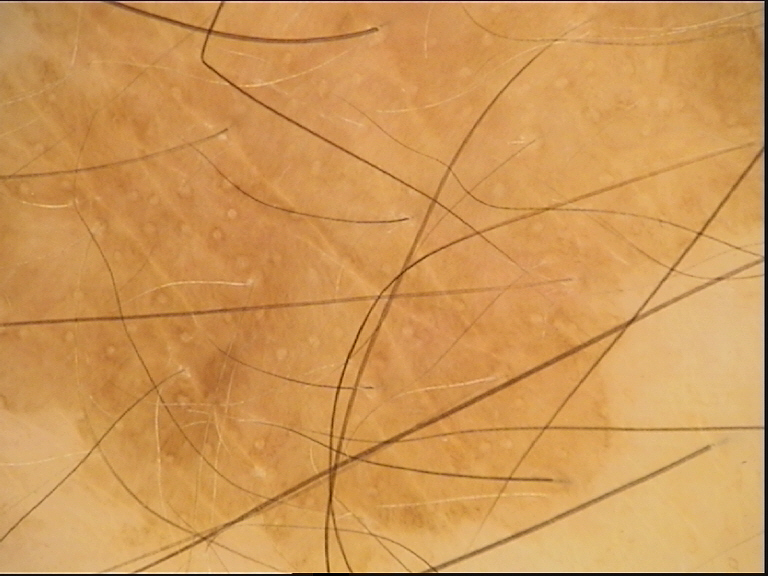classification: keratinocytic
class: seborrheic keratosis (expert consensus)